The photograph is a close-up of the affected area; located on the top or side of the foot: 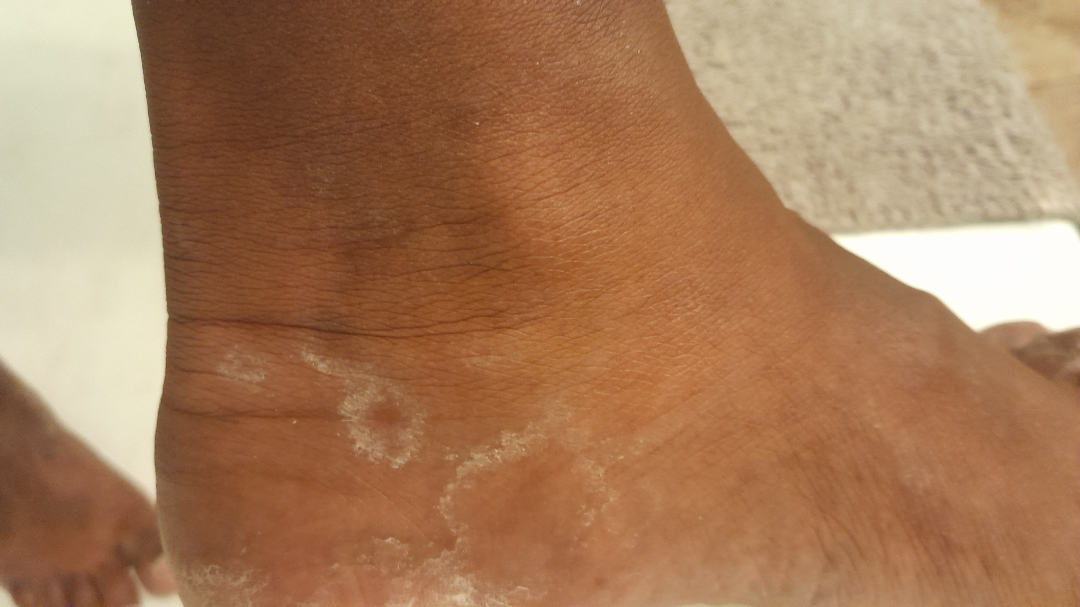assessment — unable to determine.